Dermoscopy of a skin lesion: 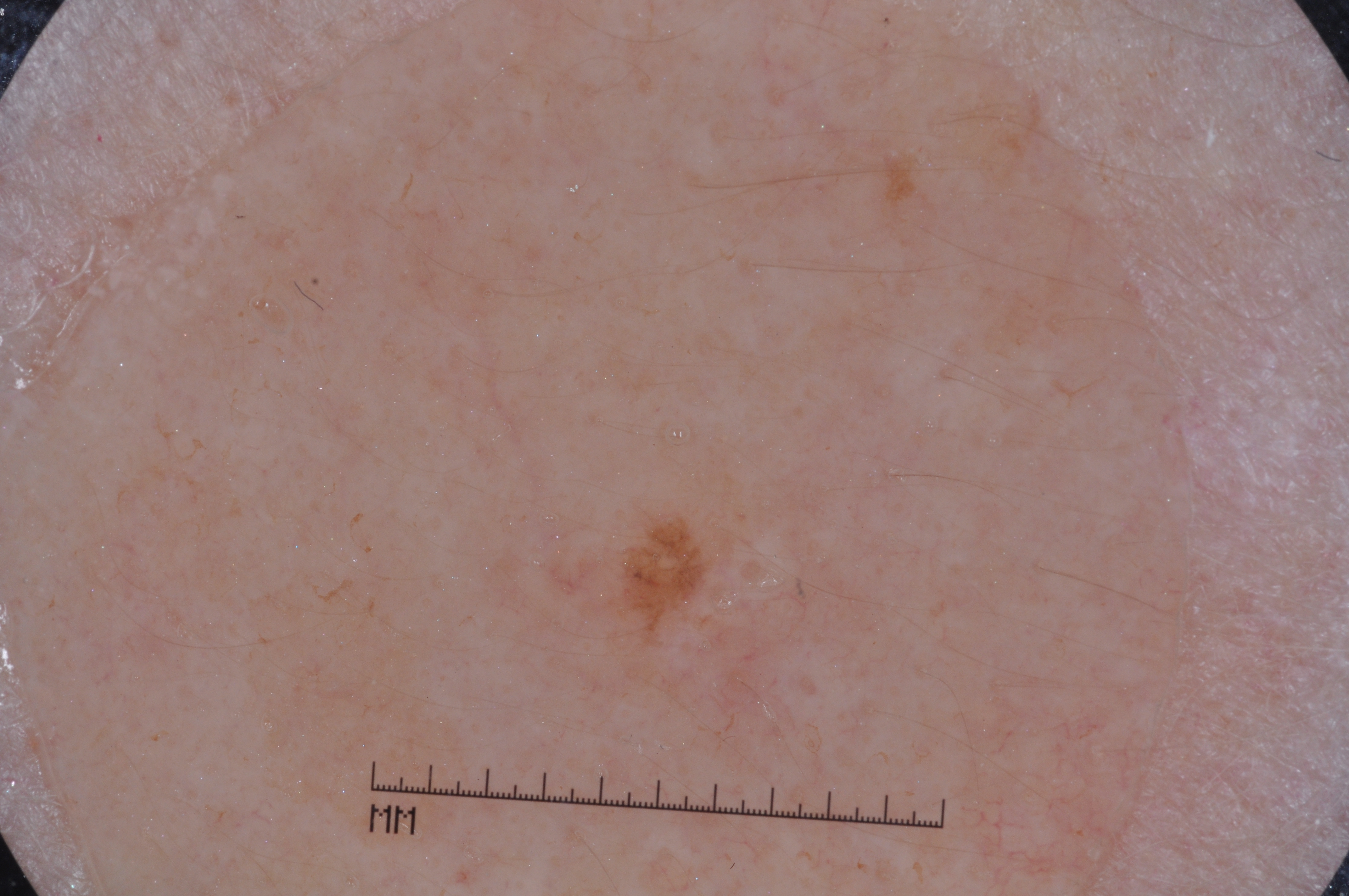| feature | finding |
|---|---|
| lesion location | box(602, 511, 715, 648) |
| absent dermoscopic features | pigment network, streaks, milia-like cysts, and negative network |
| size | ~1% of the field |
| impression | a melanocytic nevus |